The lesion involves the palm, arm and head or neck. This is a close-up image. The subject is female.
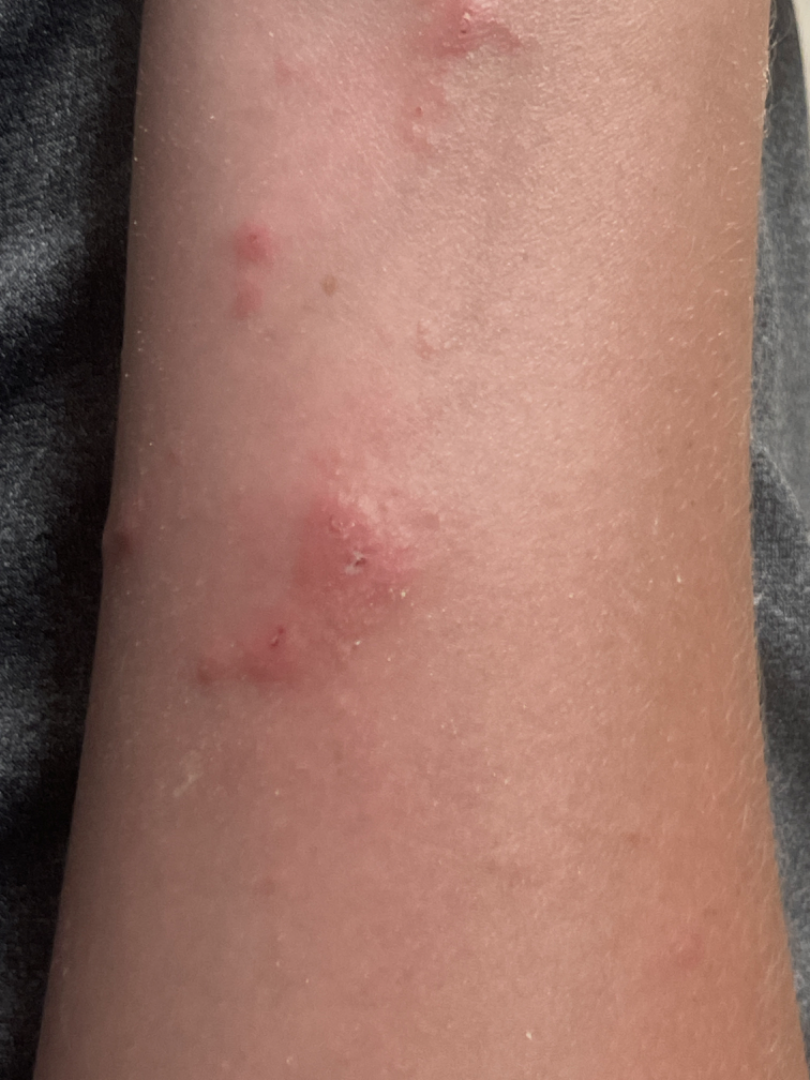Assessment:
The reviewing dermatologists' impression was: most consistent with Allergic Contact Dermatitis; less likely is Scabies; less probable is Acute dermatitis, NOS; a remote consideration is Insect Bite.